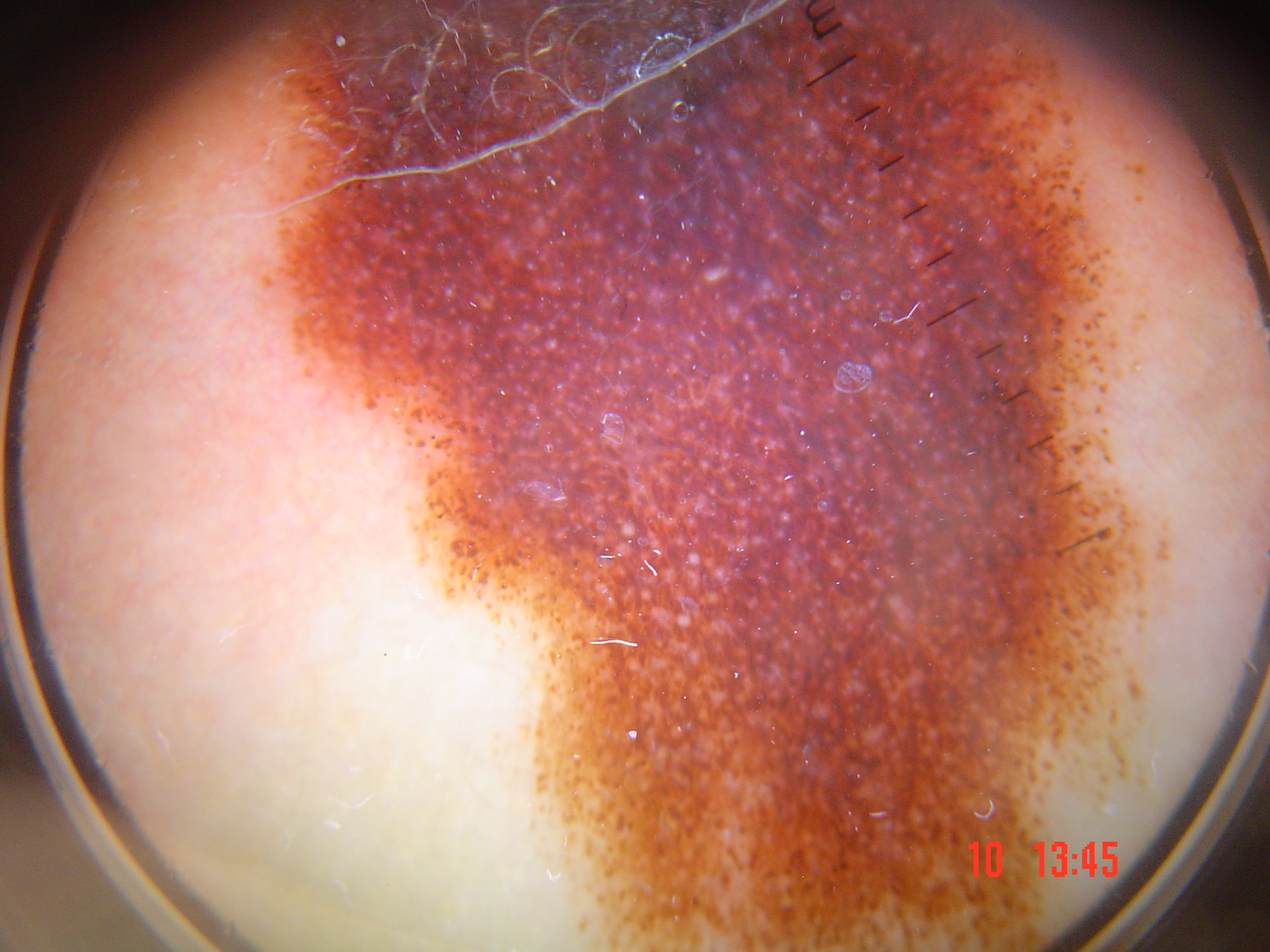Conclusion: The diagnostic label was a congenital compound nevus.